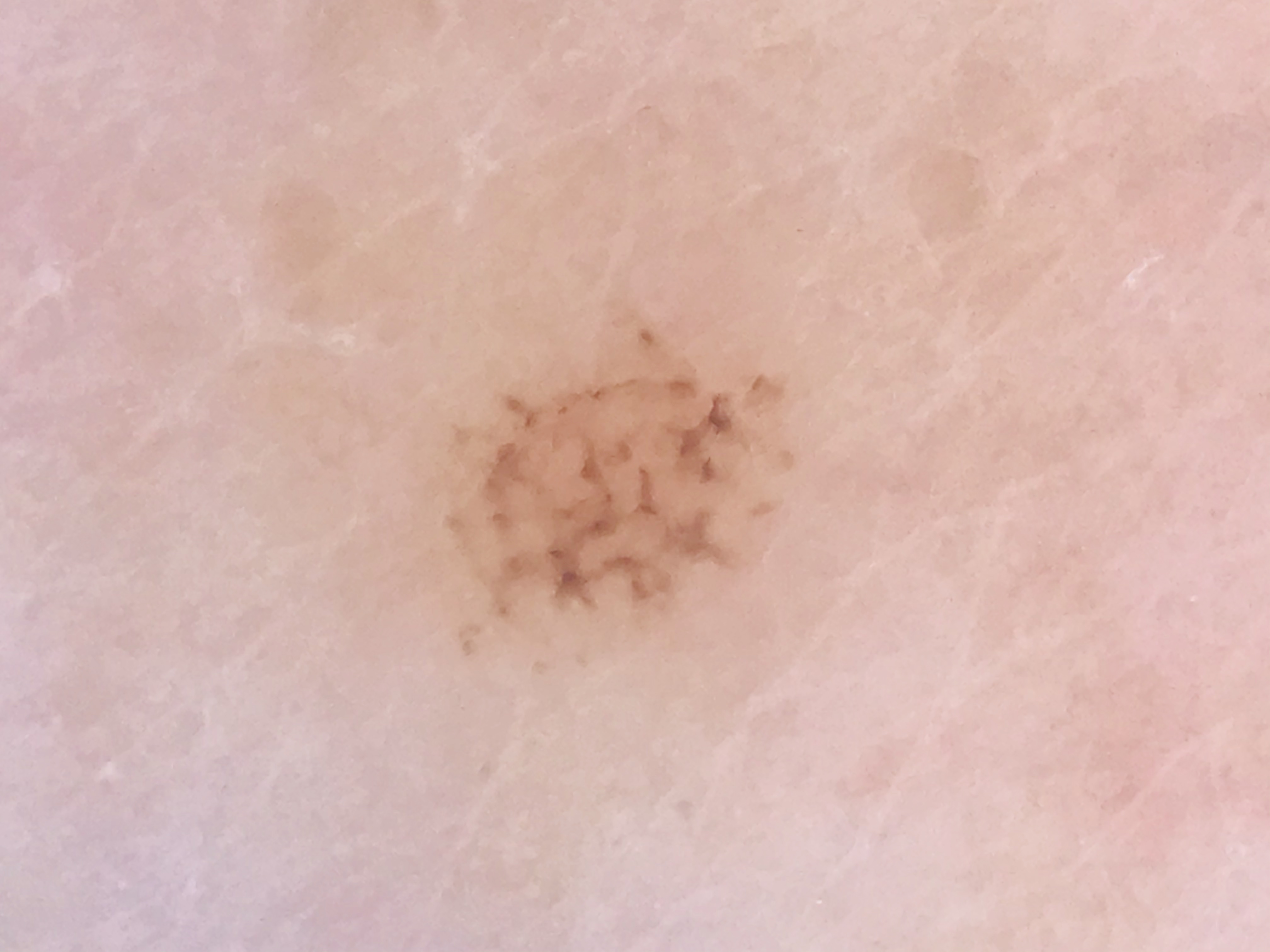diagnostic label: acral dysplastic junctional nevus (expert consensus).